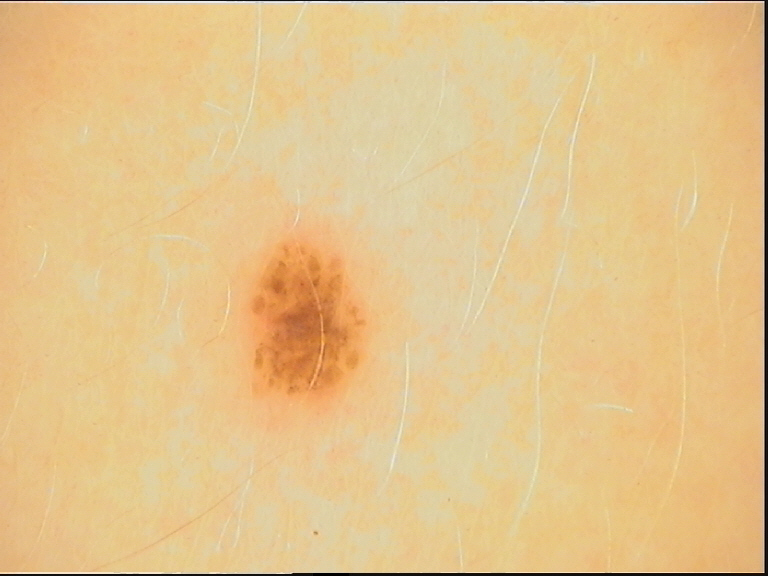Q: What is the imaging modality?
A: dermatoscopy
Q: What is the diagnosis?
A: dysplastic junctional nevus (expert consensus)